The condition has been present for about one day; self-categorized by the patient as a rash; the lesion is described as raised or bumpy; the lesion is associated with itching and enlargement; the affected area is the leg; close-up view; no associated systemic symptoms reported: 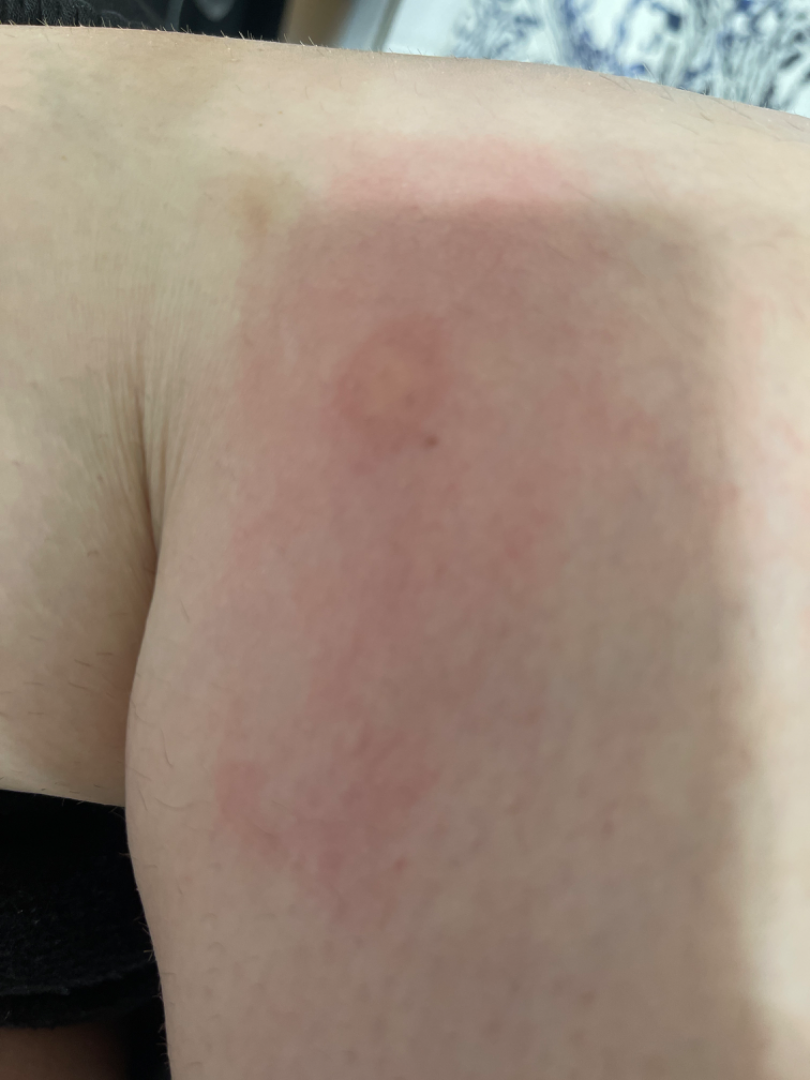assessment: could not be assessed